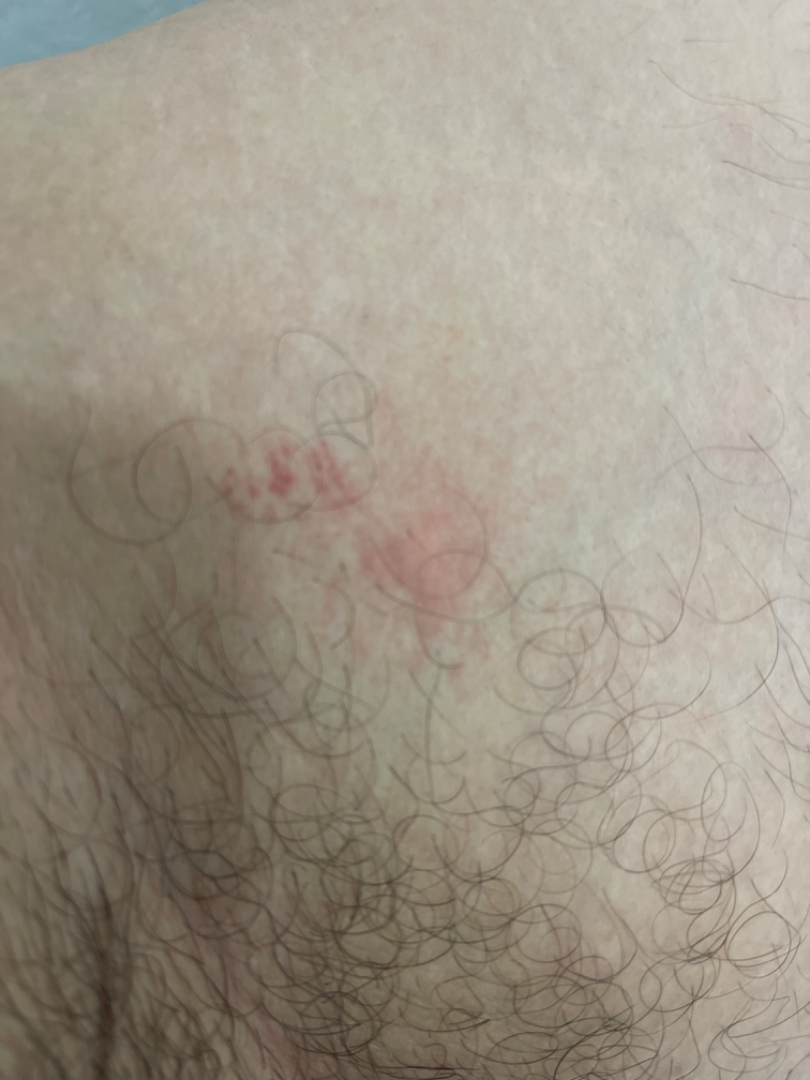A close-up photograph. The lesion involves the leg. Reported duration is less than one week. On remote dermatologist review: Eczema (100%).